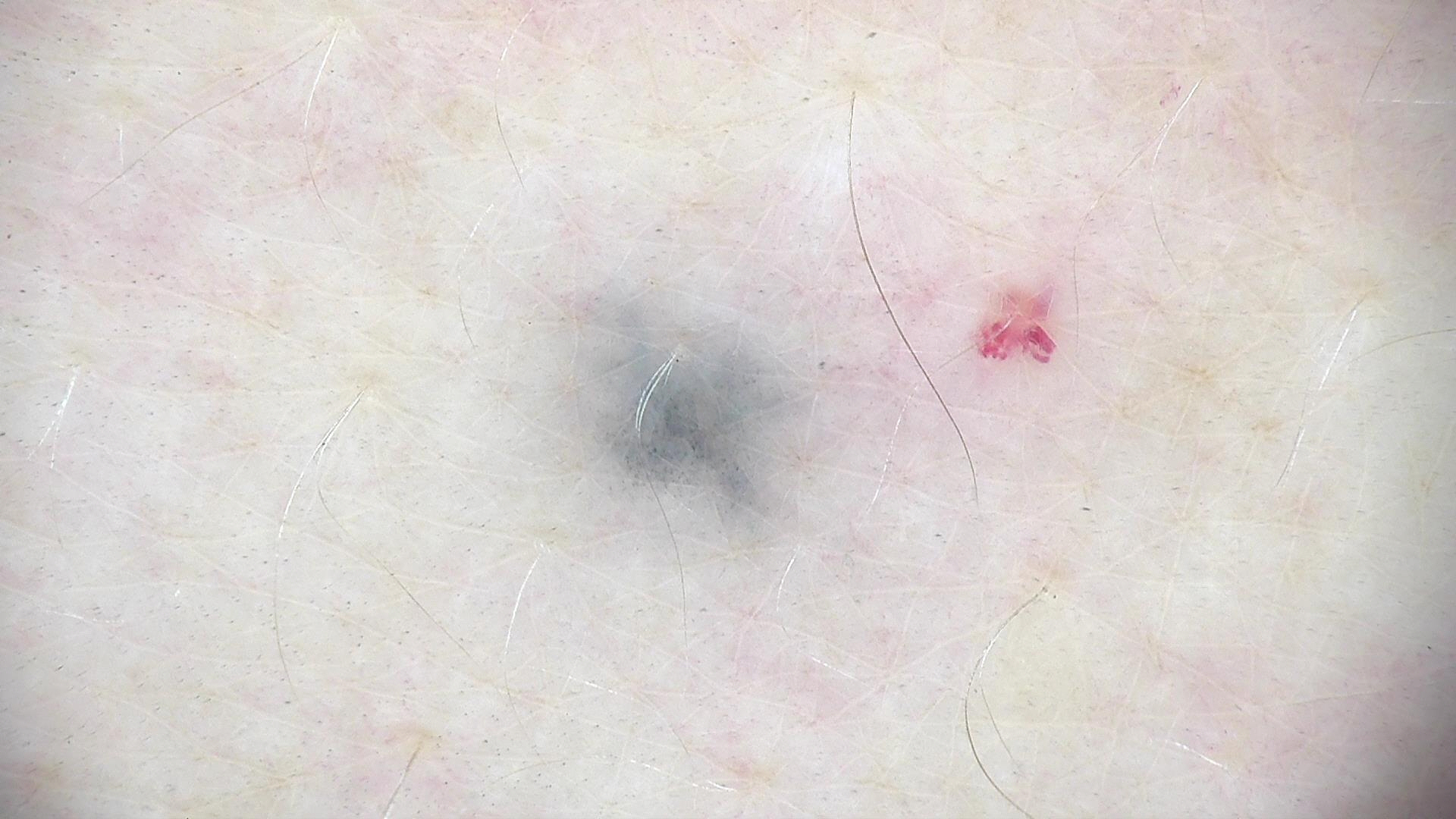Conclusion:
Classified as a blue nevus.